Contact-polarized dermoscopy of a skin lesion. A female patient aged 63-67. The patient was assessed as Fitzpatrick phototype II — 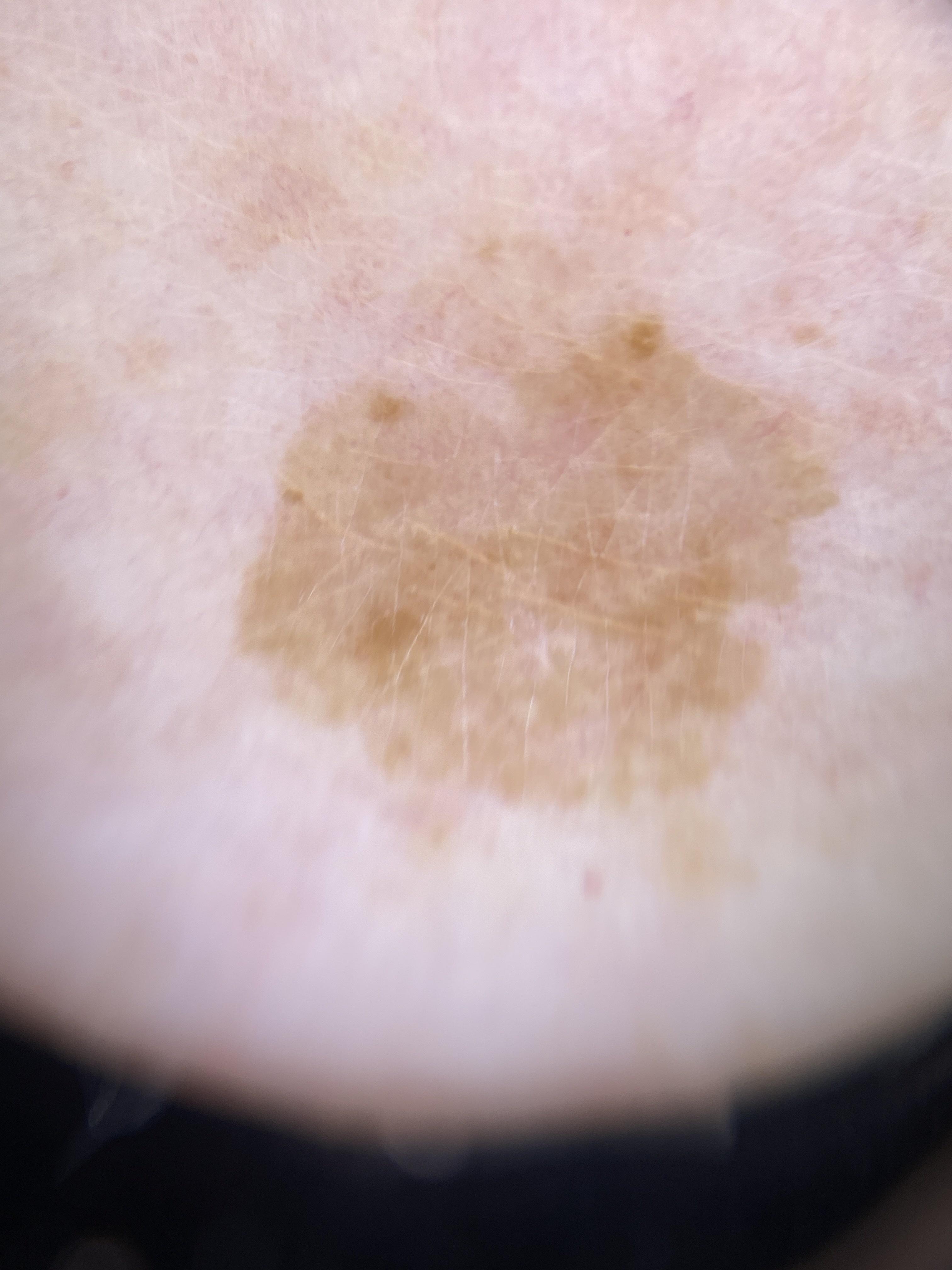The lesion was found on a lower extremity.
Clinically diagnosed as a benign lesion — a seborrheic keratosis.